A male subject, roughly 75 years of age. A dermoscopic image of a skin lesion:
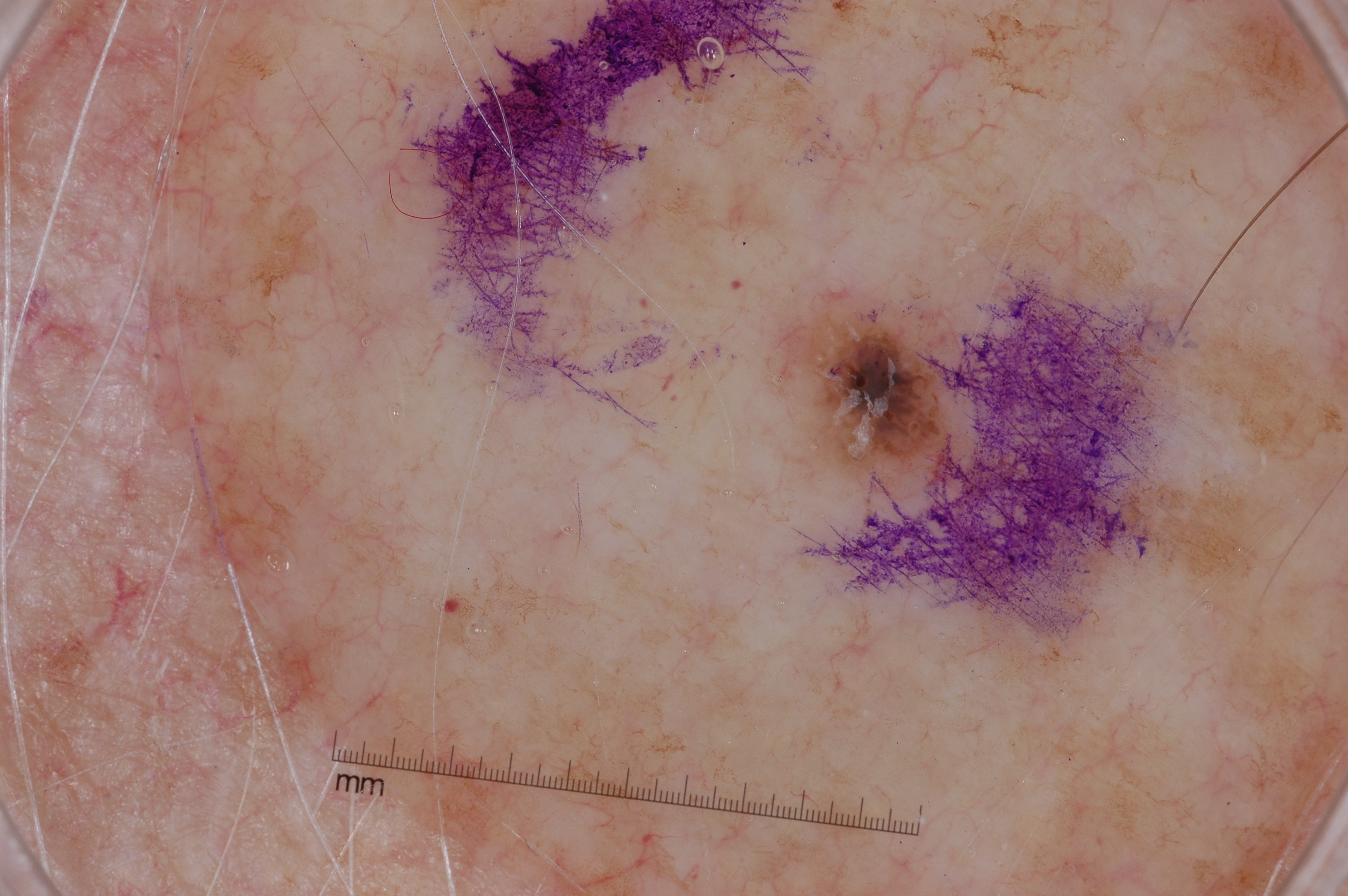Case summary: The lesion occupies the region 790/308/948/476. The lesion covers approximately 2% of the dermoscopic field. The dermoscopic pattern shows milia-like cysts; no streaks, negative network, or pigment network. Impression: Diagnosed as a seborrheic keratosis, a non-melanocytic (keratinocytic) lesion.